A dermoscopic close-up of a skin lesion:
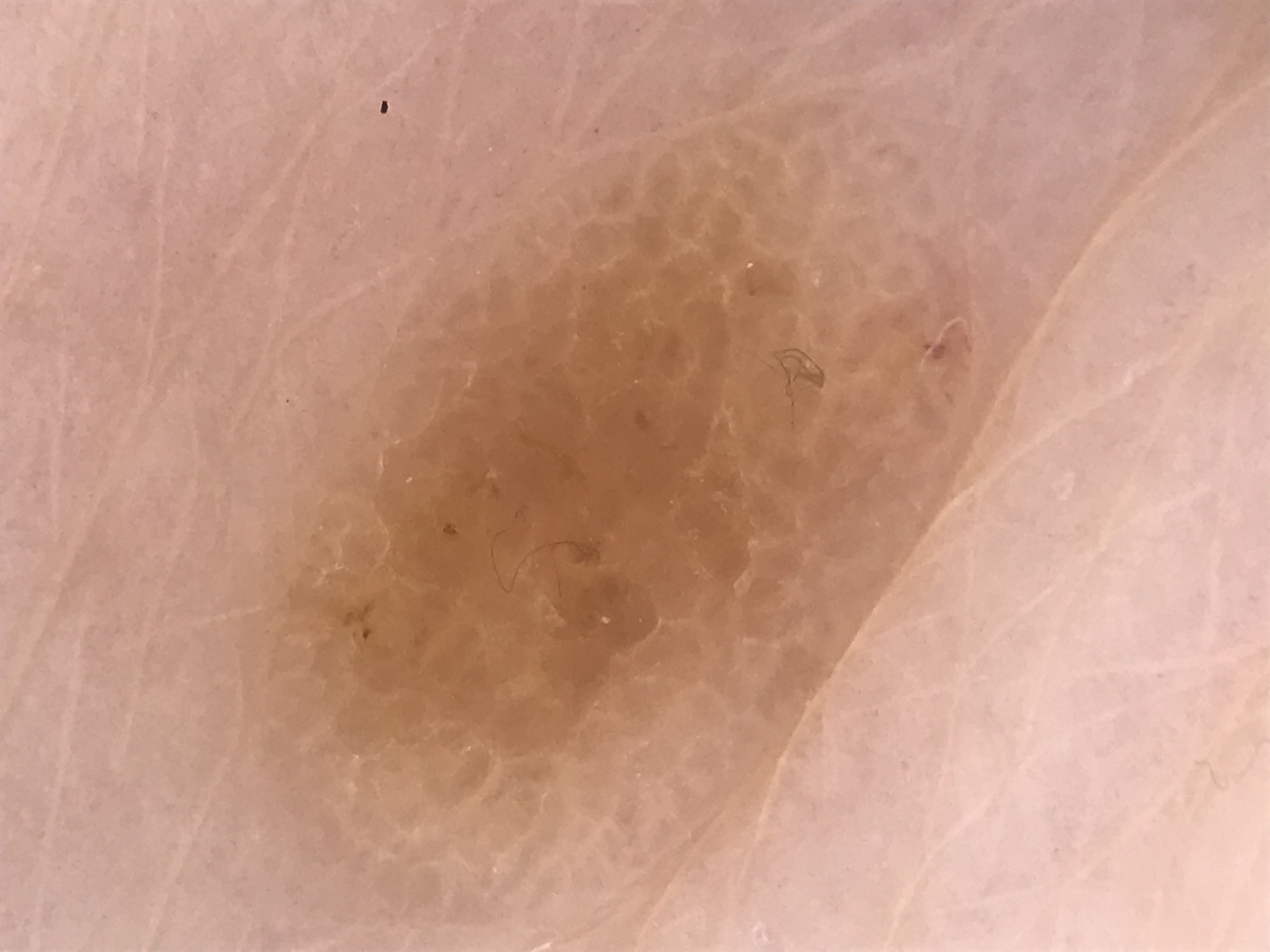| feature | finding |
|---|---|
| label | seborrheic keratosis (expert consensus) |